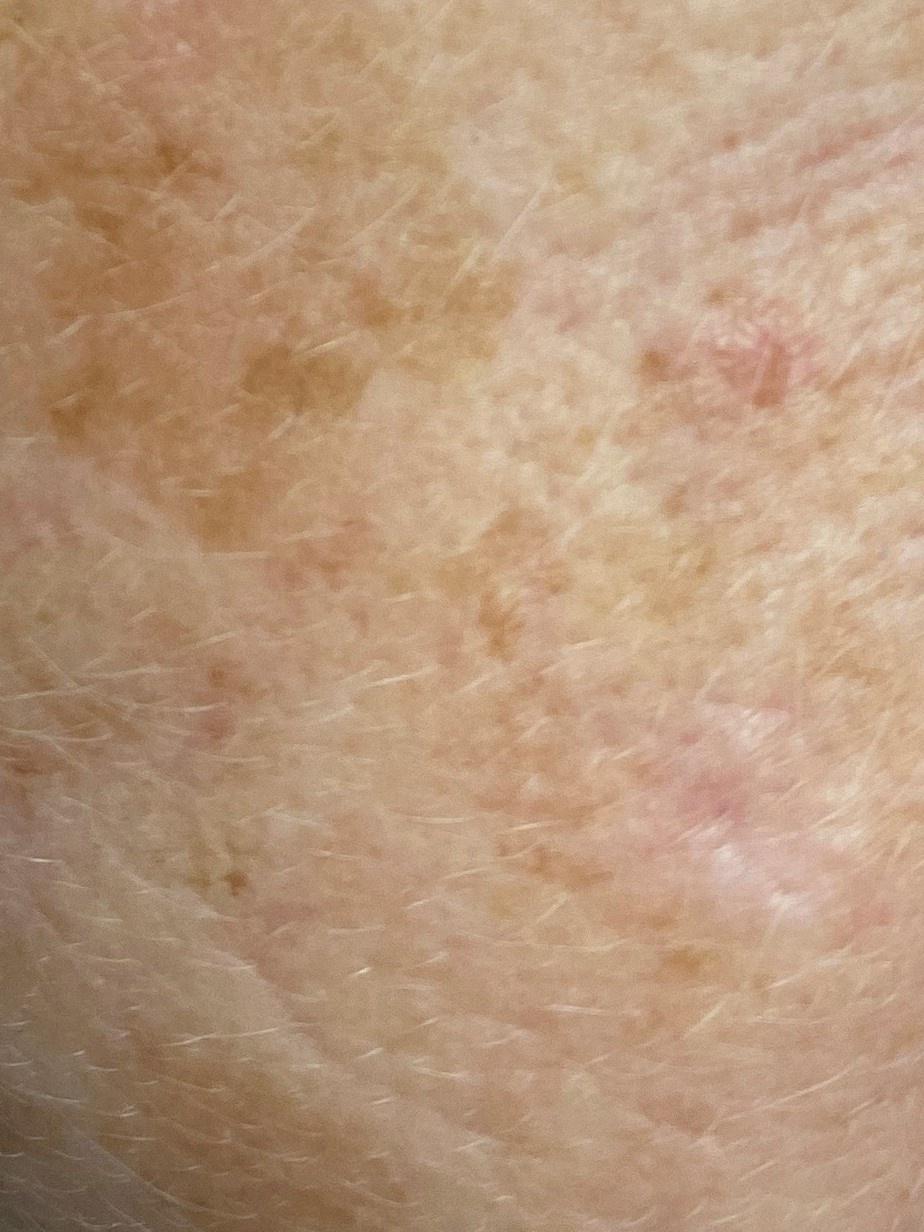Histopathology confirmed a solar or actinic keratosis.